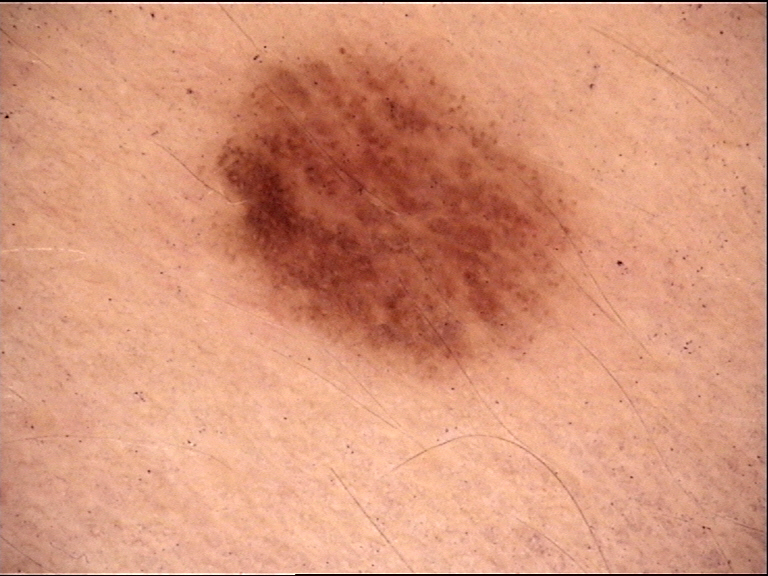Classified as a dysplastic junctional nevus.